Imaged for a research study, with no referral diagnosis recorded · the patient describes having few moles overall · the patient says their skin reddens with sun exposure · a male patient 78 years old: 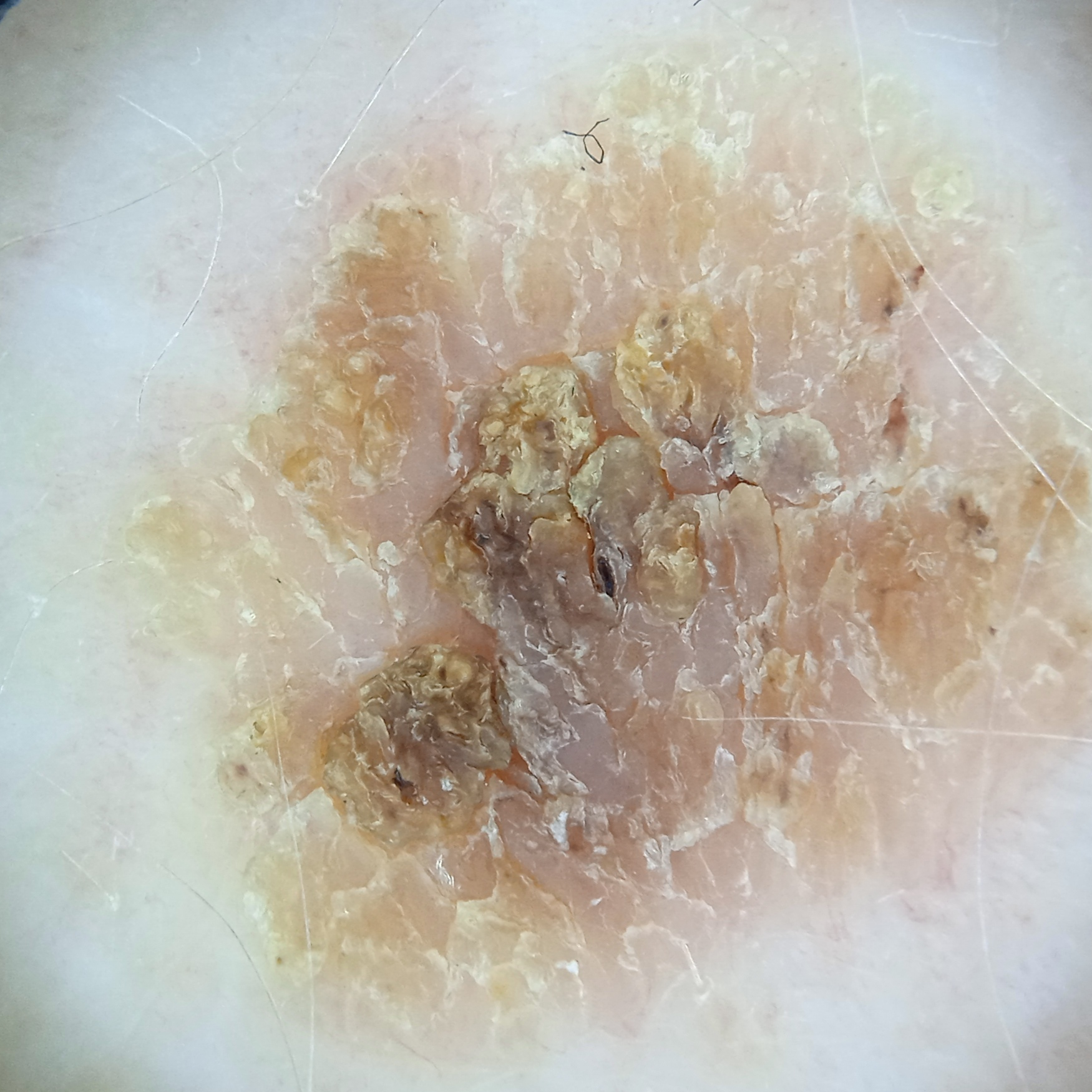Located on the back. The lesion measures approximately 11 mm. The four-dermatologist consensus diagnosis was a seborrheic keratosis; the reviewers were moderately confident; an alternative consideration was a squamous cell carcinoma.